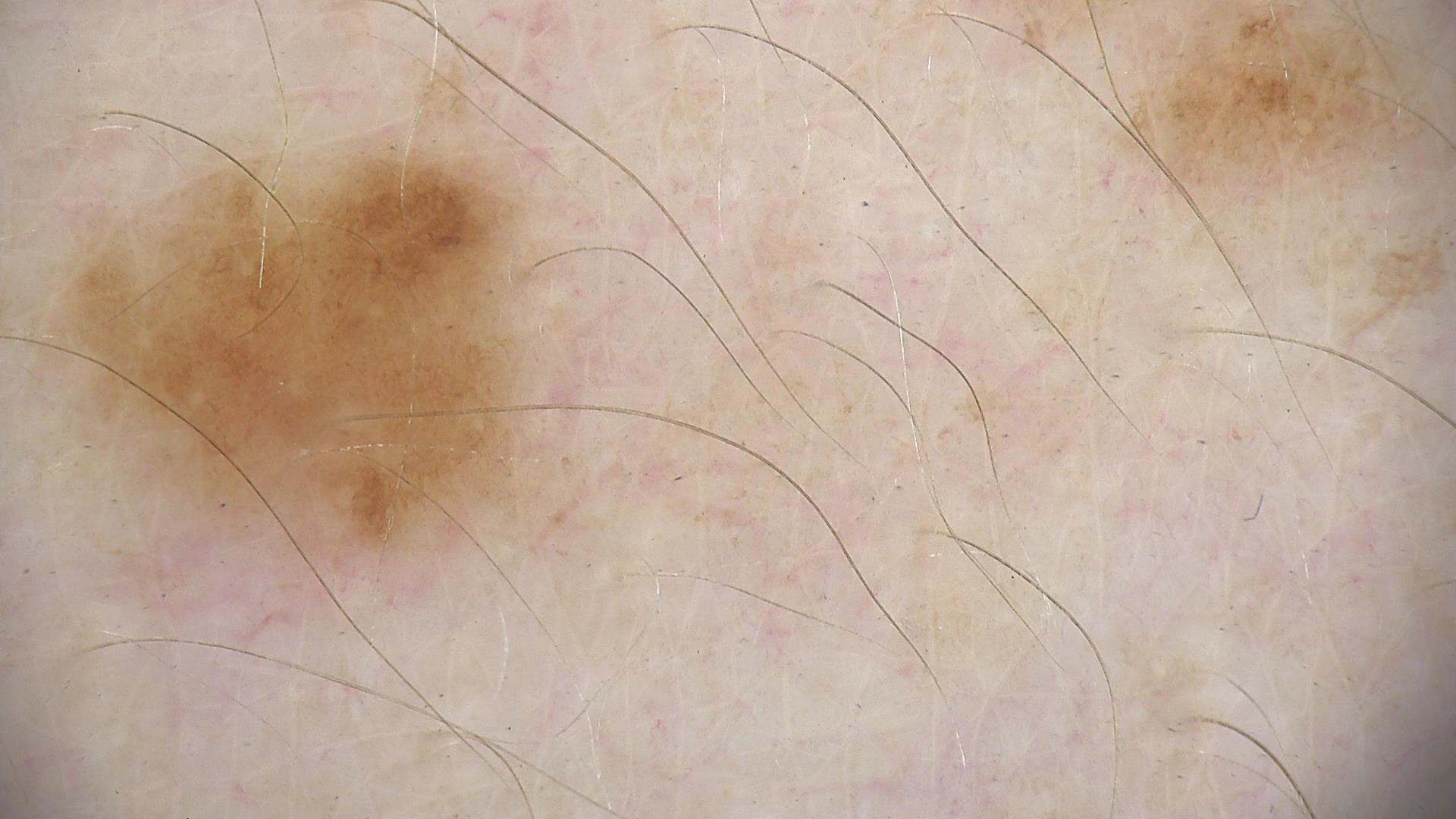{
  "diagnosis": {
    "name": "dysplastic junctional nevus",
    "code": "jd",
    "malignancy": "benign",
    "super_class": "melanocytic",
    "confirmation": "expert consensus"
  }
}